Close-up view · located on the front of the torso: 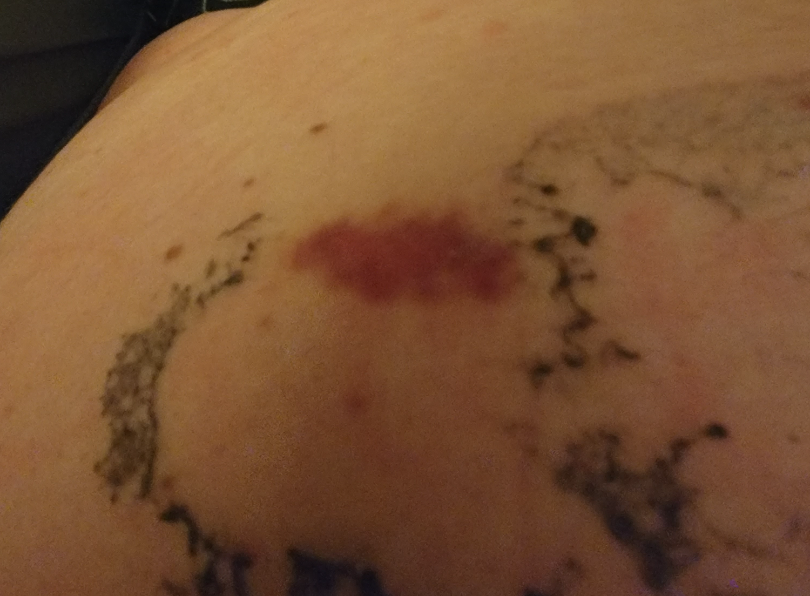{
  "assessment": "could not be assessed",
  "duration": "about one day",
  "skin_tone": {
    "monk_skin_tone": 3
  },
  "symptoms": "bothersome appearance",
  "texture": "flat"
}